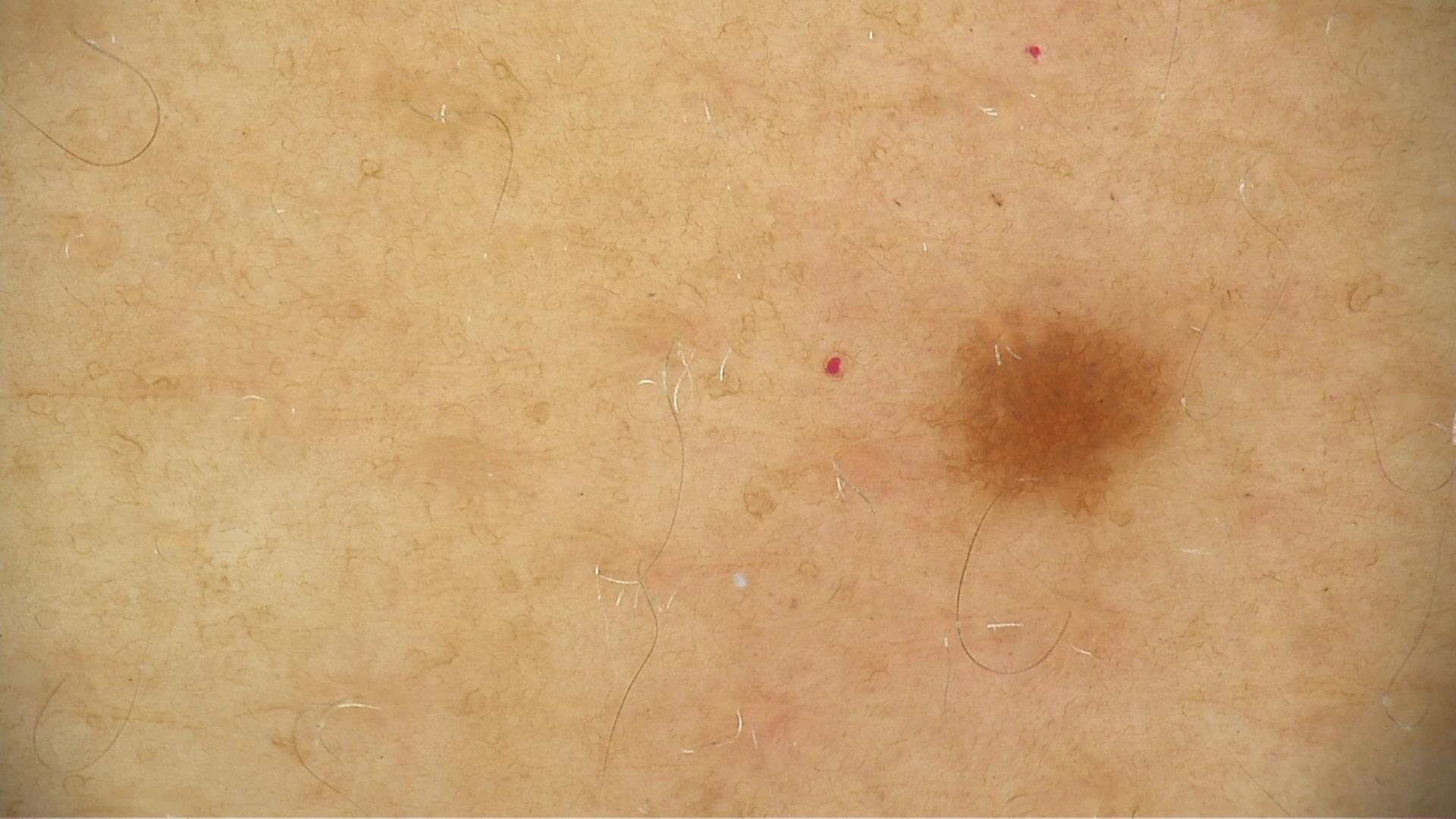Dermoscopy of a skin lesion. The diagnosis was a dysplastic junctional nevus.